Dermoscopy of a skin lesion. A female patient aged approximately 15.
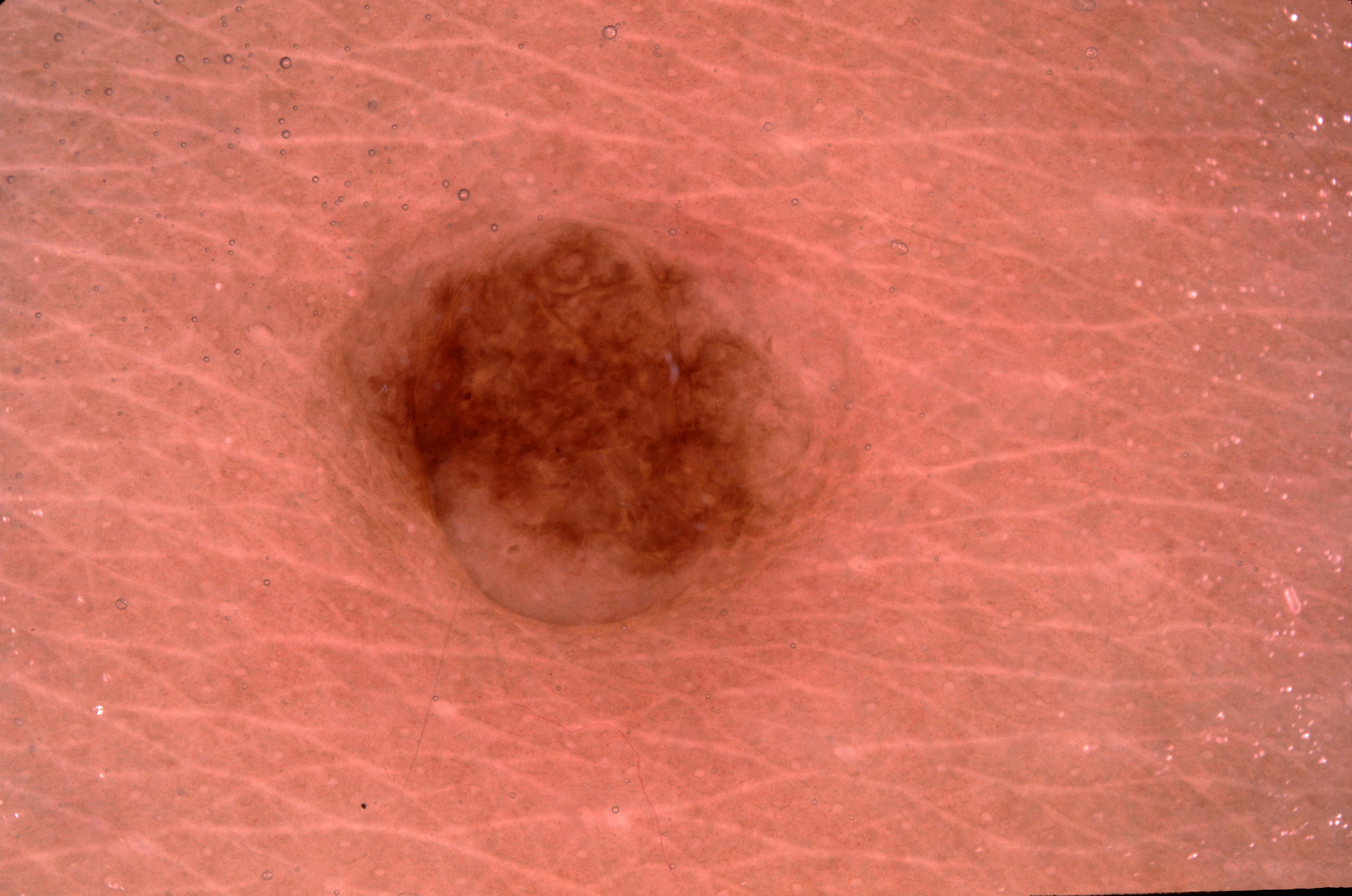The dermoscopic pattern shows no streaks, milia-like cysts, pigment network, or negative network.
The lesion occupies the region bbox(338, 224, 824, 630).
The diagnostic assessment was a melanocytic nevus.